A dermoscopic photograph of a skin lesion: 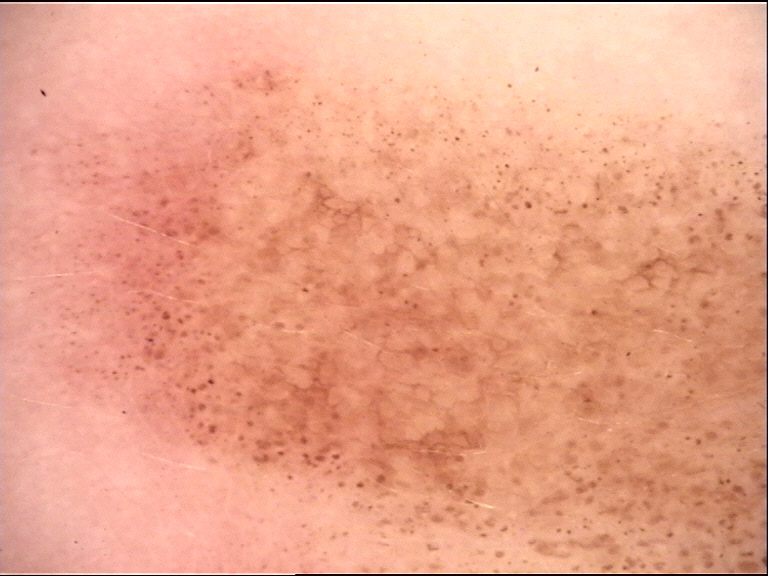Case:
The morphology is that of a banal lesion.
Impression:
Classified as a congenital junctional nevus.